A close-up photograph:
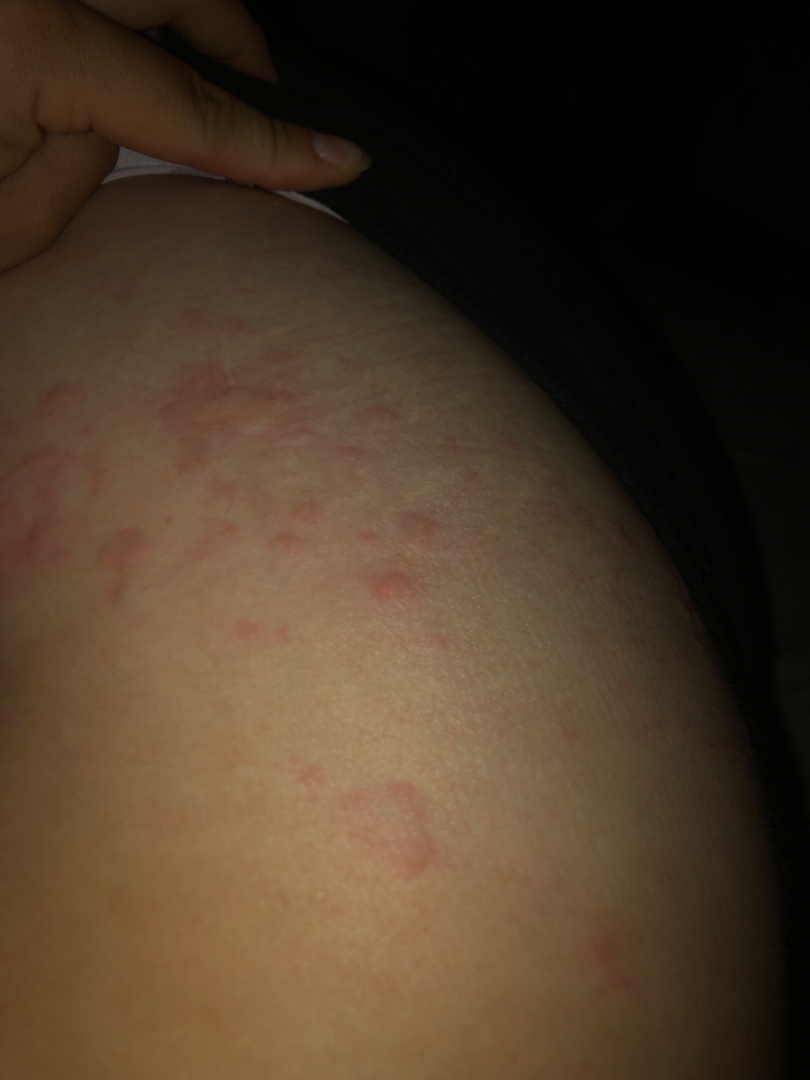diagnostic considerations: favoring Urticaria.